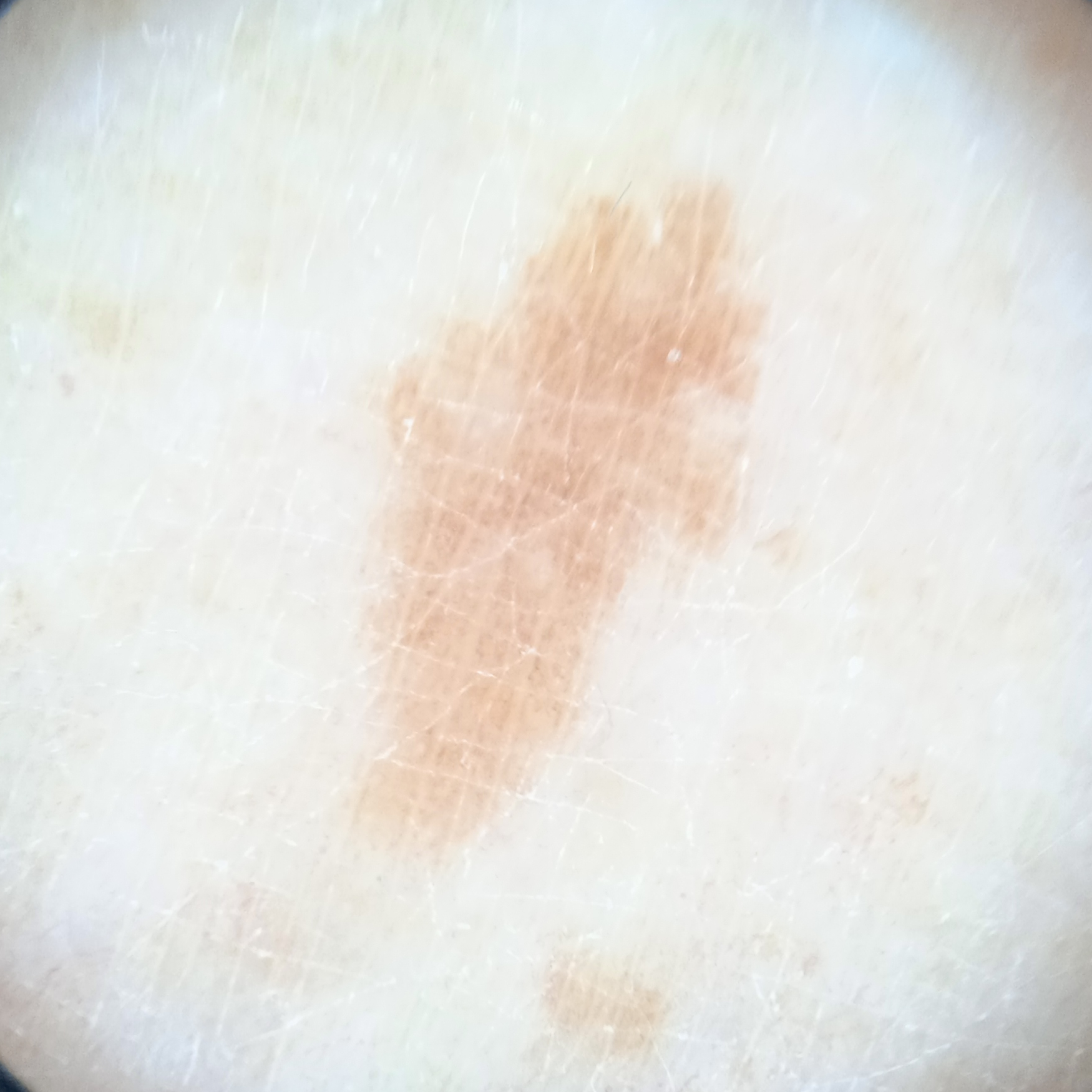A female subject 75 years old.
On a questionnaire the patient reported a personal history of skin cancer and a personal history of cancer.
The patient describes having a moderate number of moles.
Collected as part of a research study, without a referral diagnosis.
A dermoscopic image of a skin lesion.
The patient says their skin tans without first burning.
The lesion is on a leg.
The lesion measures approximately 8.2 mm.
The lesion was assessed as a melanocytic nevus.